A dermoscopic image of a skin lesion · the patient says their skin reddens with sun exposure · a female subject aged 26 · the patient describes having numerous moles · acquired for a research image collection, with no referral diagnosis · on a questionnaire the patient reported a history of sunbed use.
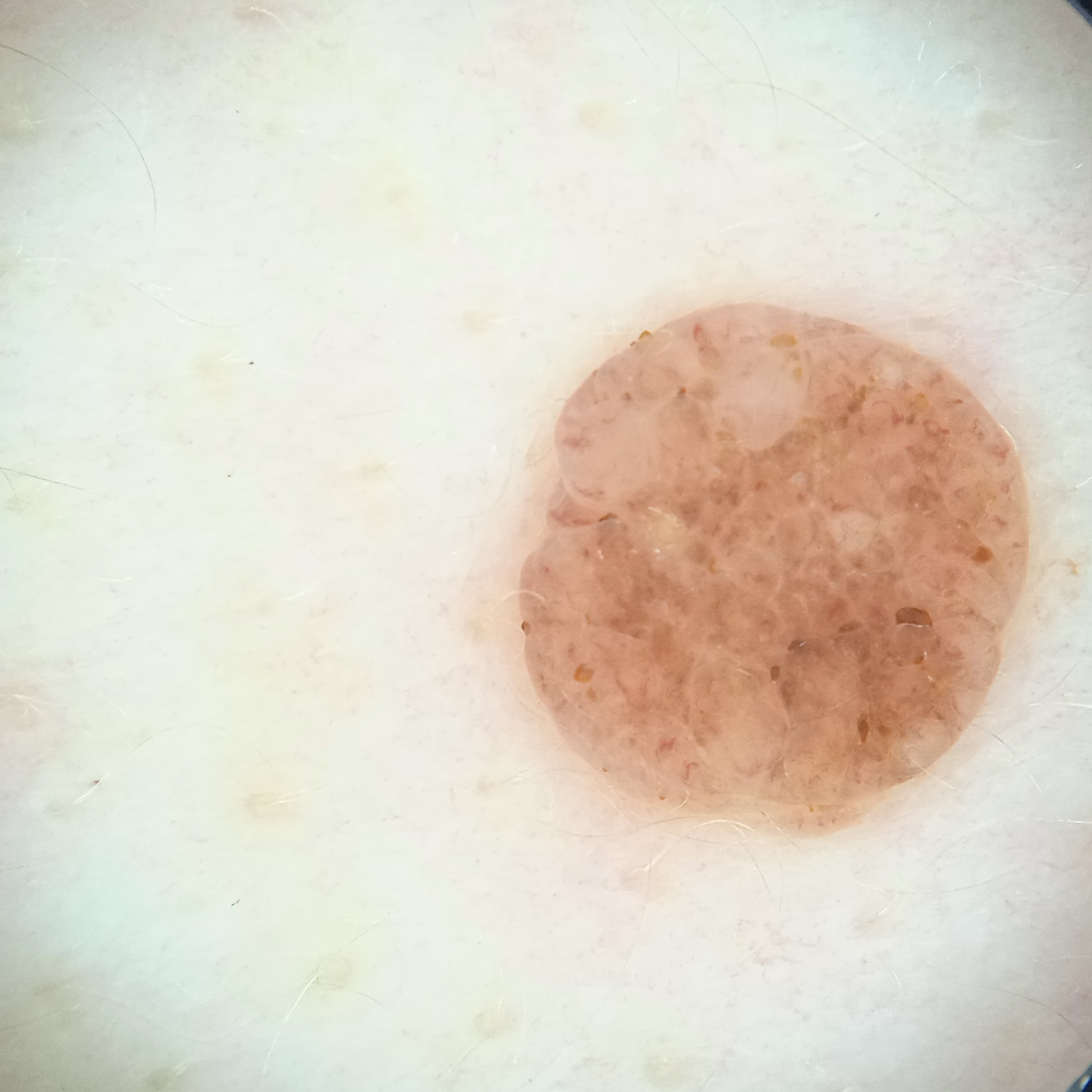The lesion is on the back. The lesion measures approximately 5.6 mm. The diagnostic impression was a melanocytic nevus.